The affected area is the leg. Texture is reported as raised or bumpy. Lay graders estimated MST 2. The photo was captured at an angle. The patient notes the condition has been present for less than one week. No associated systemic symptoms reported. Reported lesion symptoms include bothersome appearance and itching. The contributor is 18–29, female:
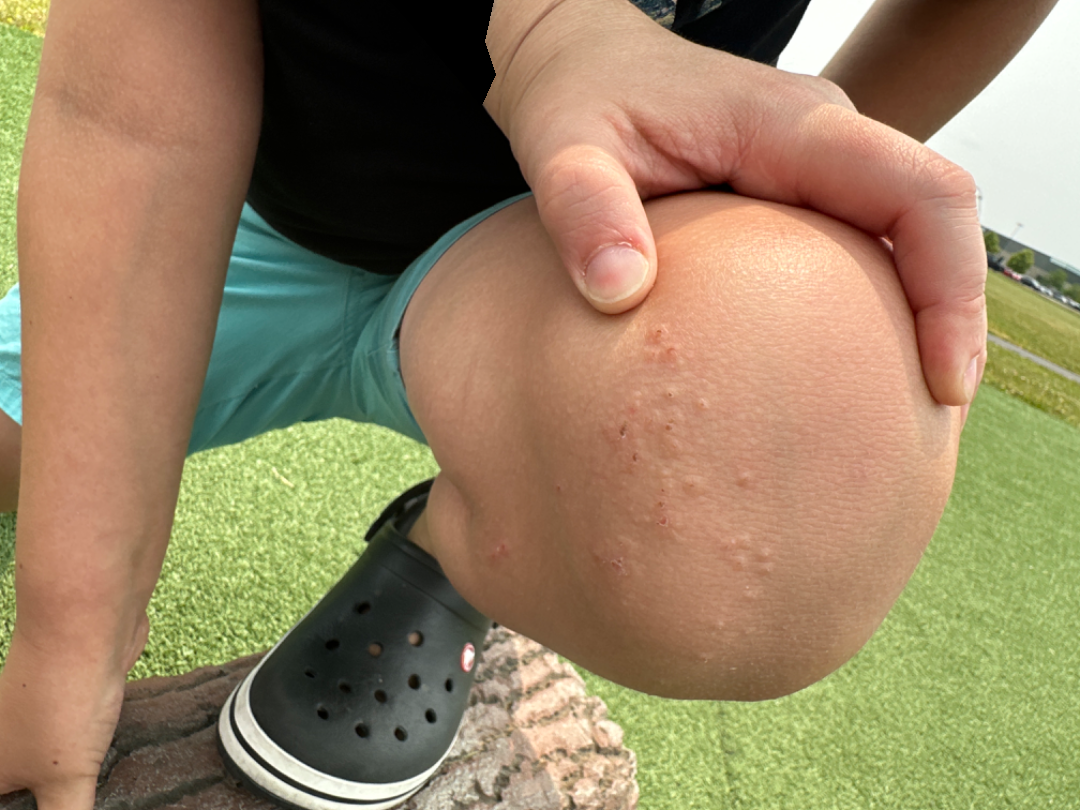The case was indeterminate on photographic review.